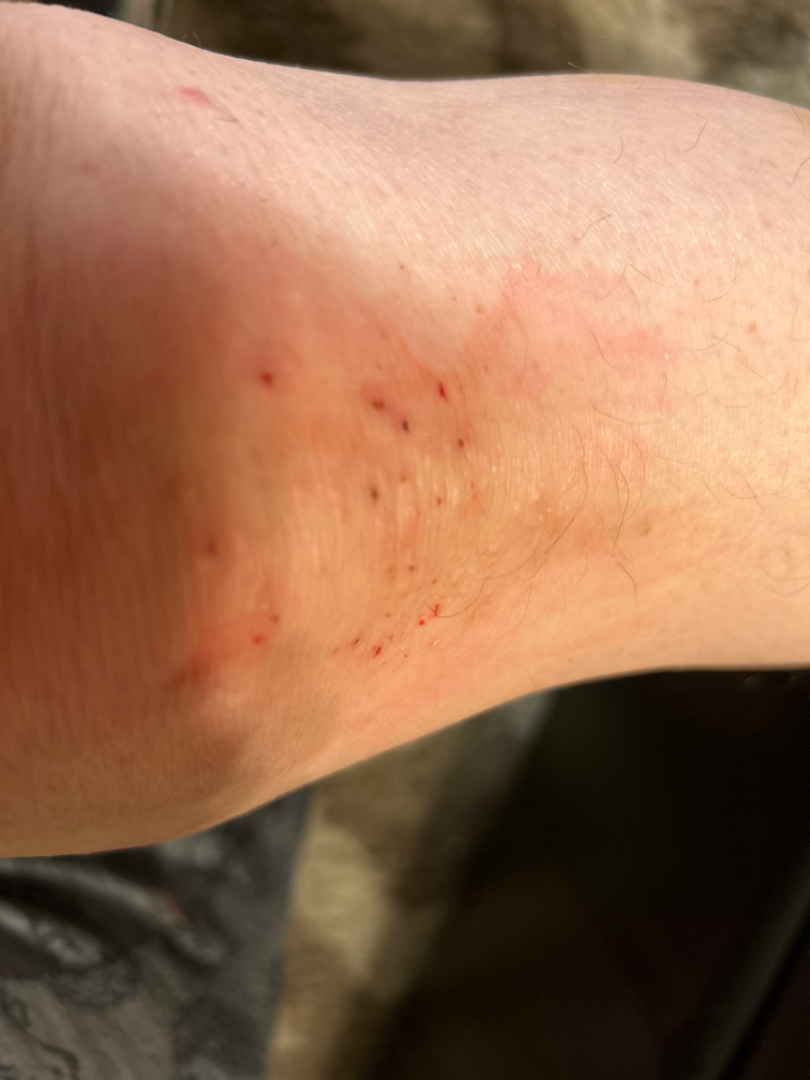The patient considered this a rash. This image was taken at an angle. Reported lesion symptoms include itching and burning. Texture is reported as raised or bumpy. The reviewing clinician's impression was: Eczema and Dermatitis herpetiformis were each considered, in no particular order.